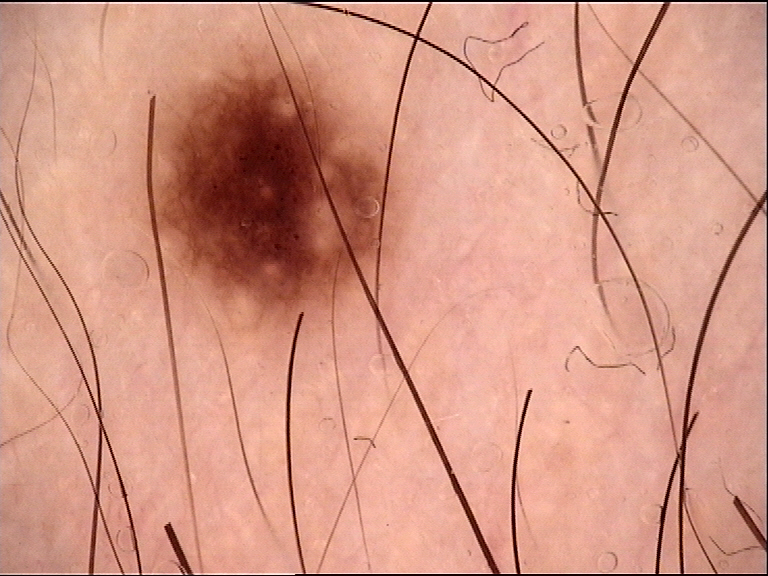The diagnostic label was a junctional nevus.